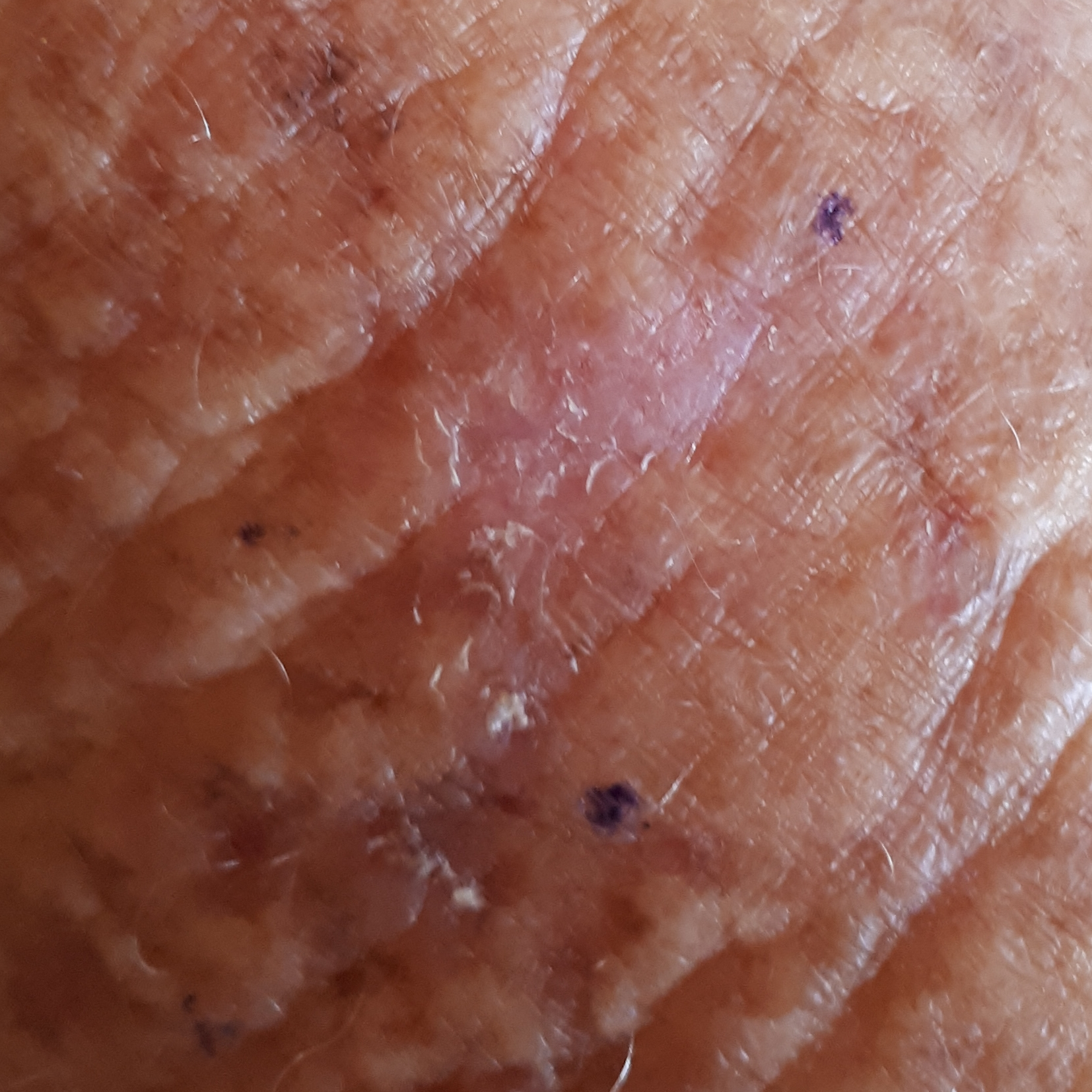Case:
- subject — female, 63 years old
- skin type — II
- imaging — clinical photograph
- risk factors — prior skin cancer (patient or family), pesticide exposure
- body site — a forearm
- lesion size — 19x12 mm
- symptoms — growth
- impression — actinic keratosis (clinical consensus)